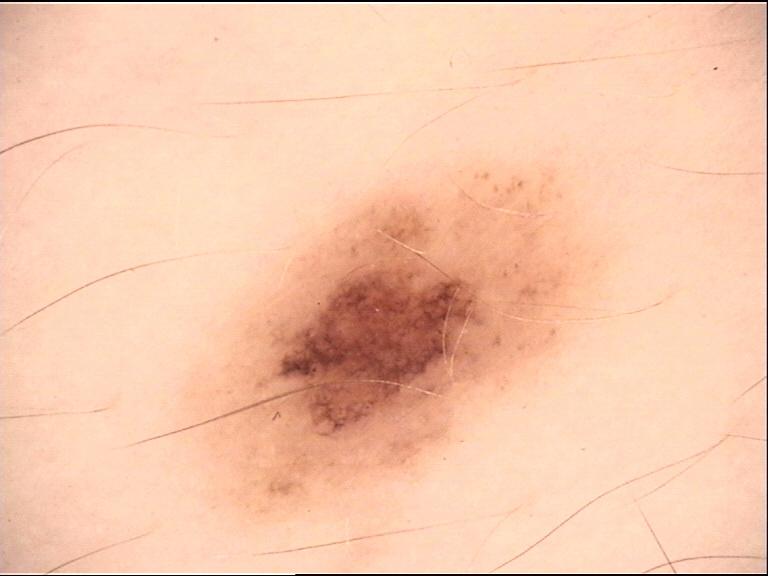Q: What kind of image is this?
A: dermatoscopy
Q: What is the diagnosis?
A: dysplastic junctional nevus (expert consensus)